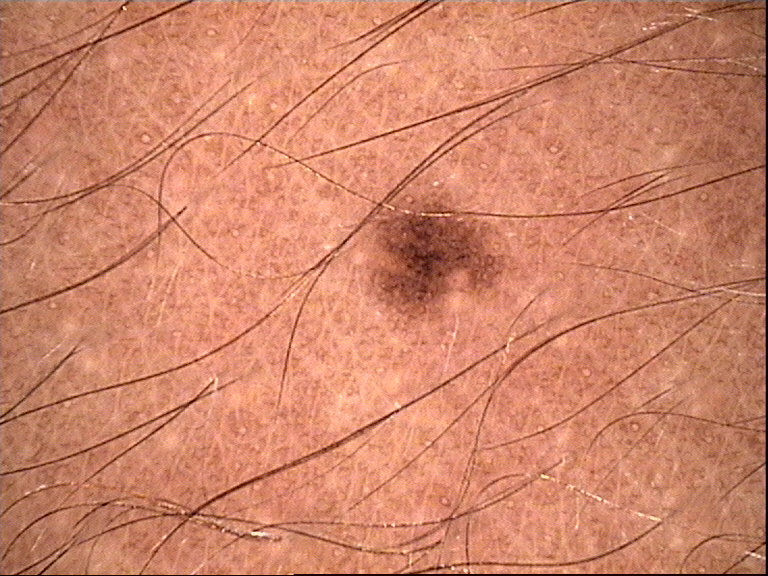diagnostic label=dysplastic junctional nevus (expert consensus)